A dermoscopic close-up of a skin lesion.
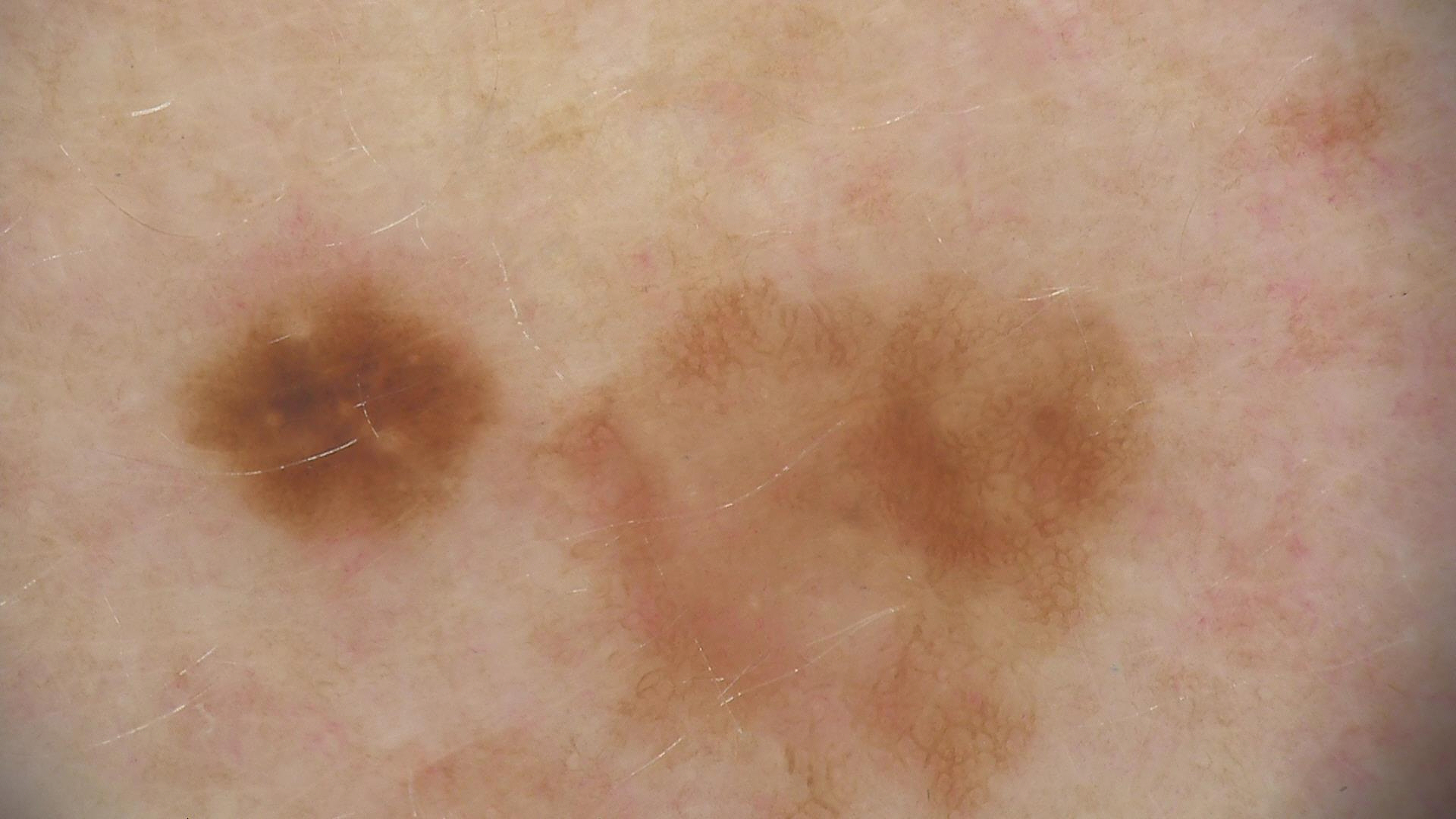Impression:
Classified as a benign lesion — a dysplastic junctional nevus.